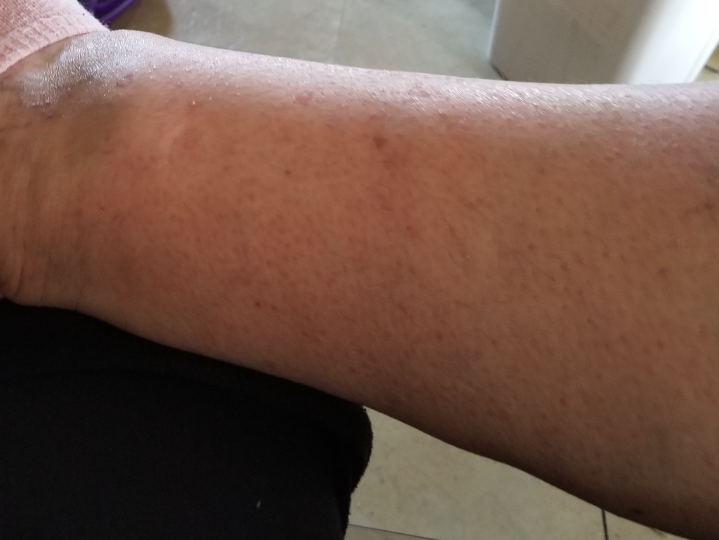Findings: A single dermatologist reviewed the case: the differential includes Stasis Dermatitis, Eczema and Allergic Contact Dermatitis, with no clear leading consideration.